The lesion involves the leg; the photograph was taken at an angle.
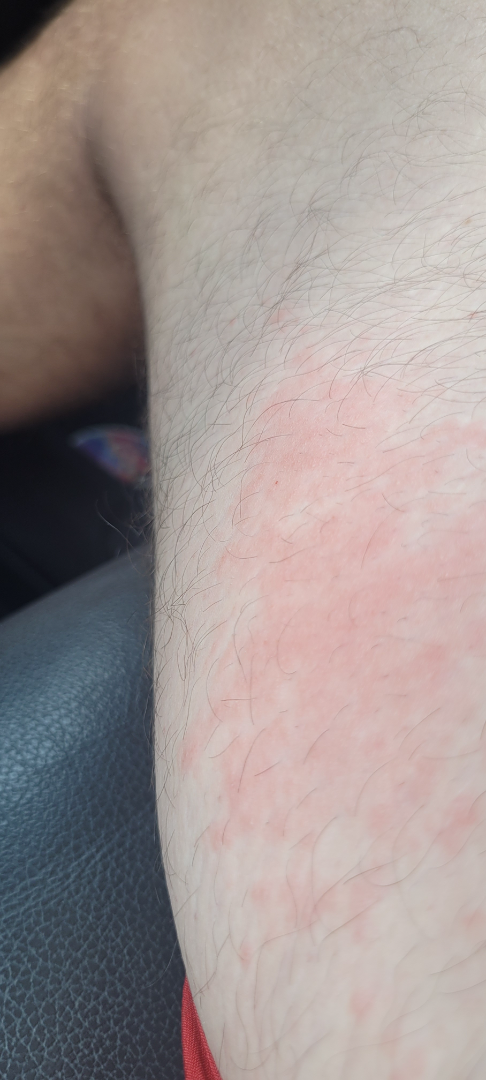Q: What was the assessment?
A: ungradable on photographic review